A female patient aged 61 — 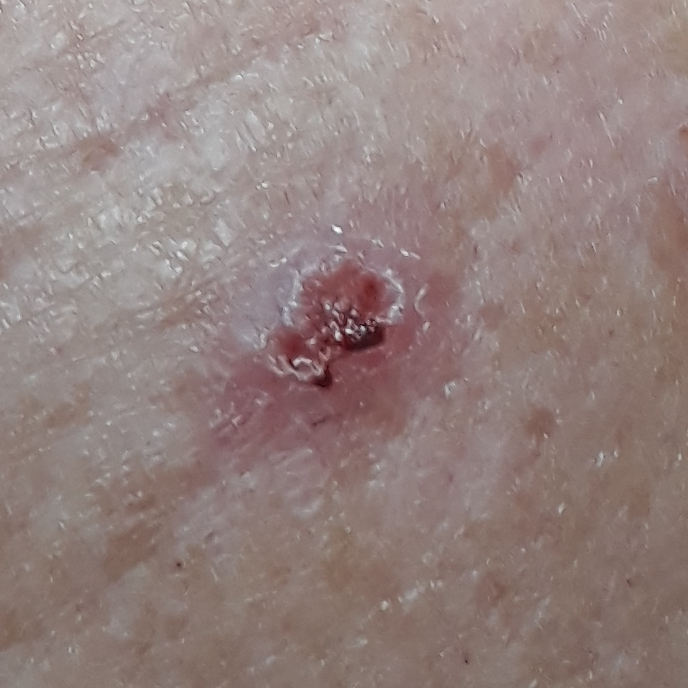body site: a forearm; diagnostic label: basal cell carcinoma (biopsy-proven).